A clinical photograph showing a skin lesion. A patient aged 49: 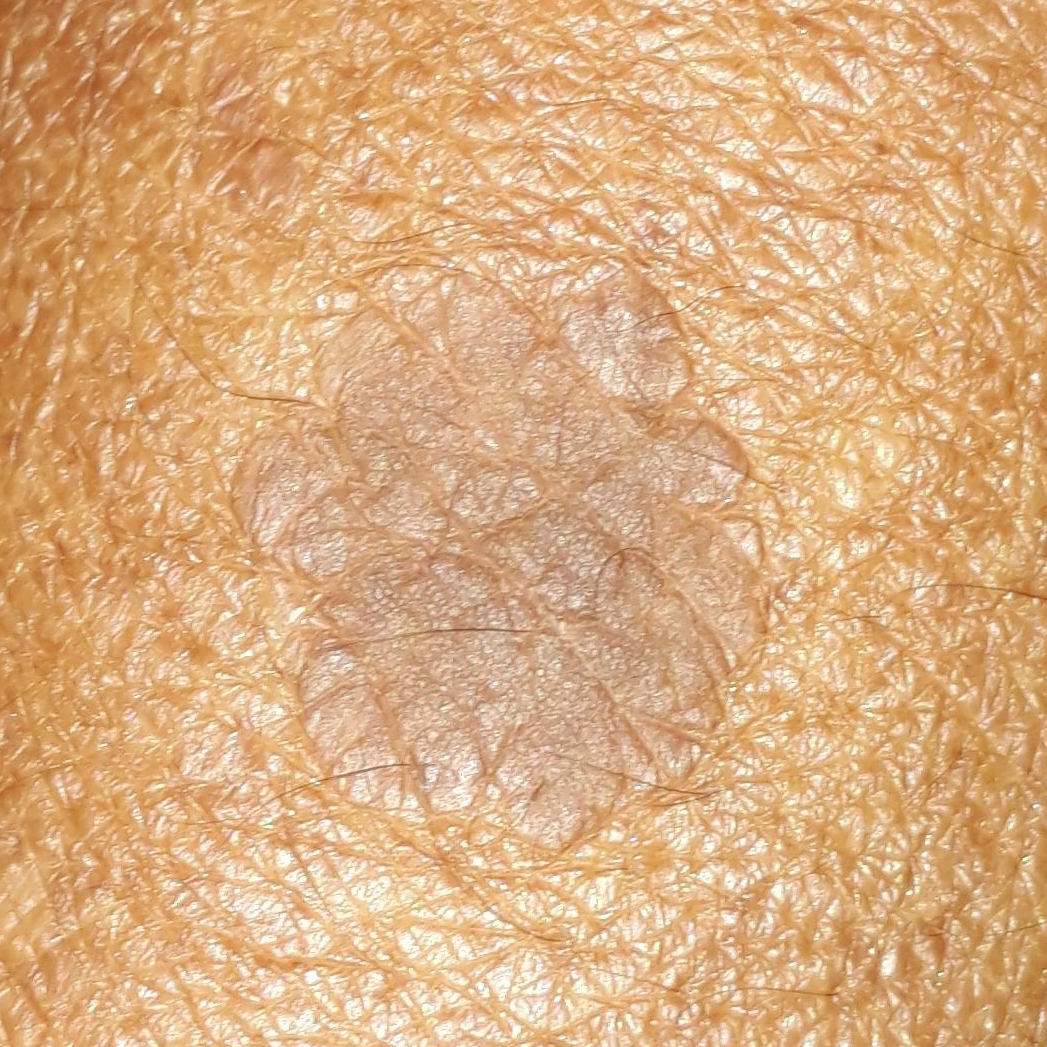The lesion involves a forearm.
Per patient report, the lesion is elevated.
Clinically diagnosed as a seborrheic keratosis.